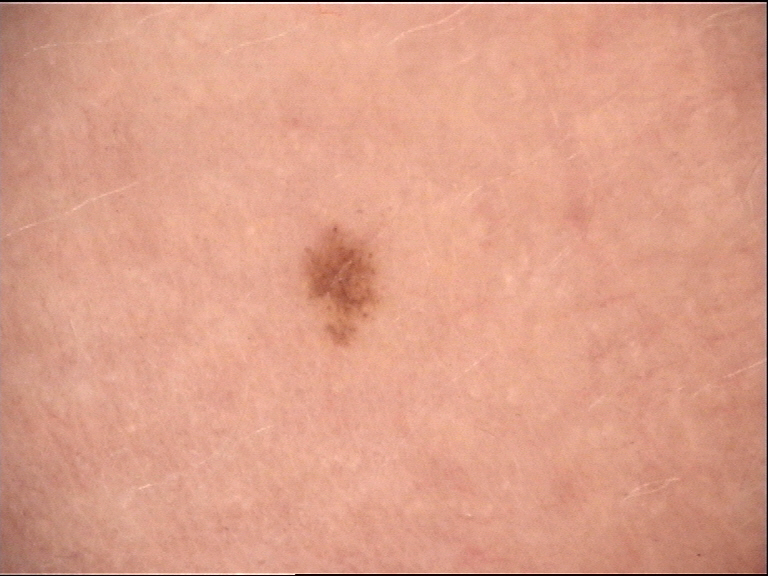Labeled as a junctional nevus.